This is a close-up image; the affected area is the arm; female contributor, age 30–39 — 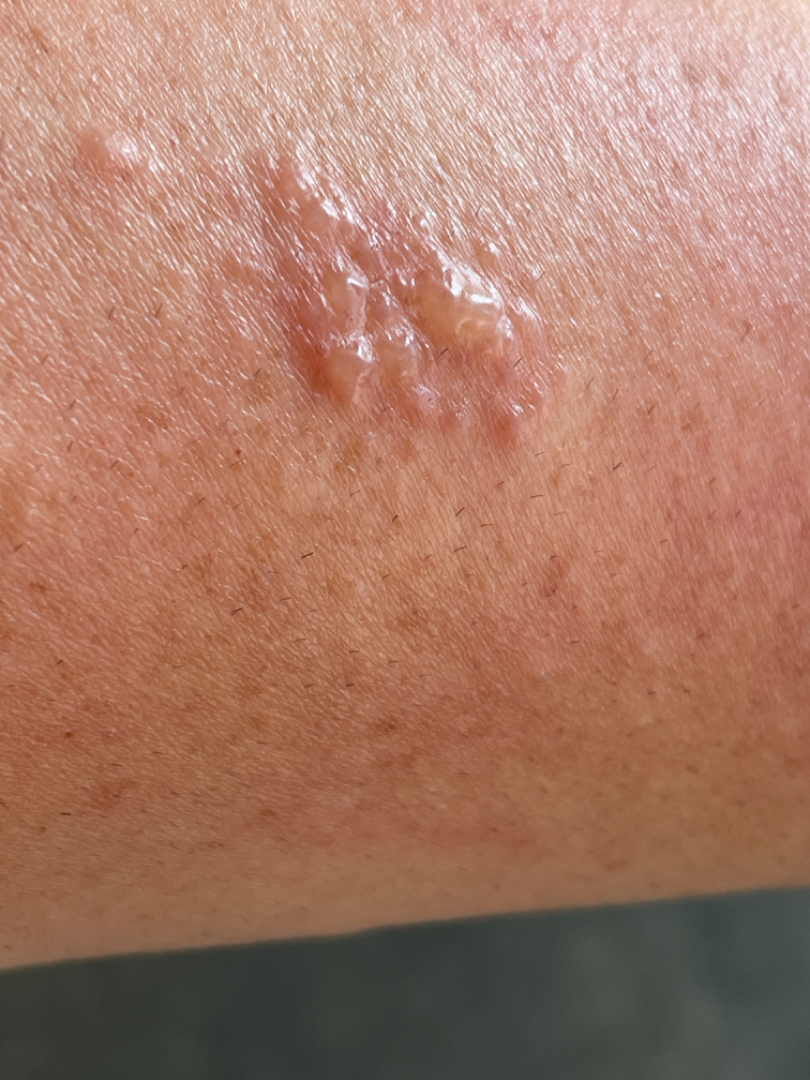On remote dermatologist review, the favored diagnosis is Herpes Simplex; also consider Allergic Contact Dermatitis; possibly Herpes Zoster; lower on the differential is Lymphangioma.